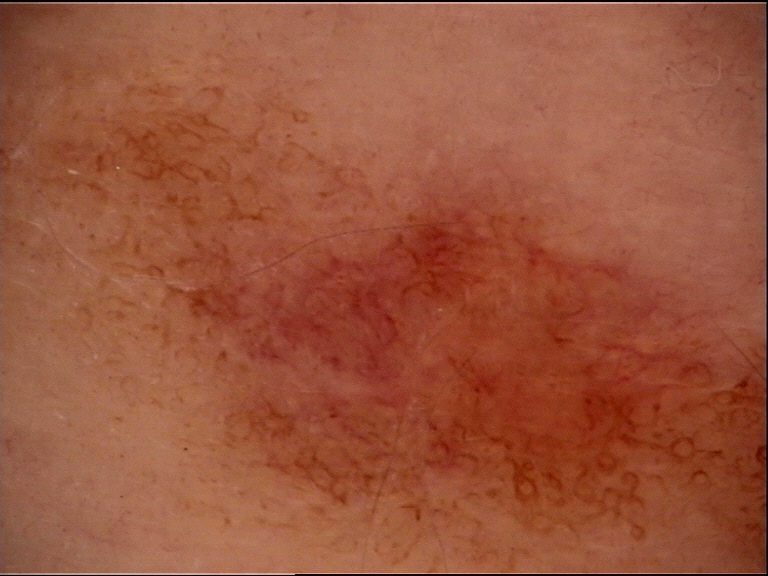A dermoscopic close-up of a skin lesion. The diagnostic label was a benign lesion — a dysplastic junctional nevus.